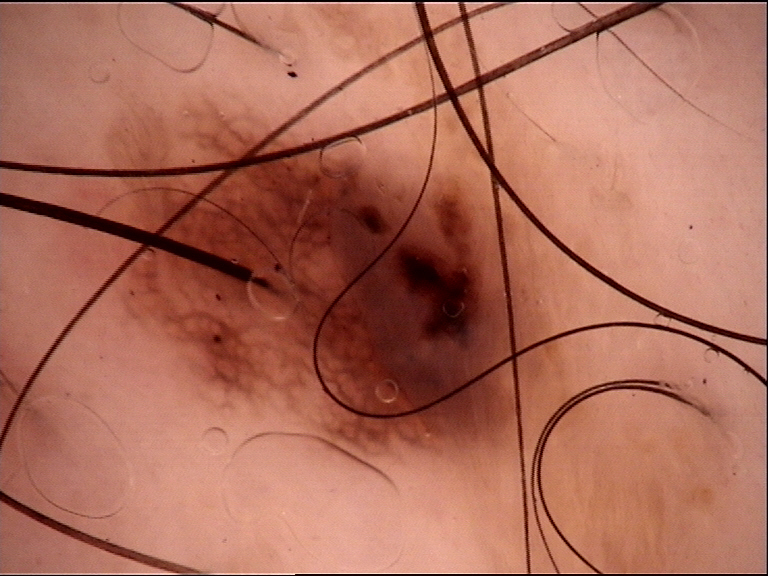{
  "diagnosis": {
    "name": "dysplastic junctional nevus",
    "code": "jd",
    "malignancy": "benign",
    "super_class": "melanocytic",
    "confirmation": "expert consensus"
  }
}